This is a close-up image: 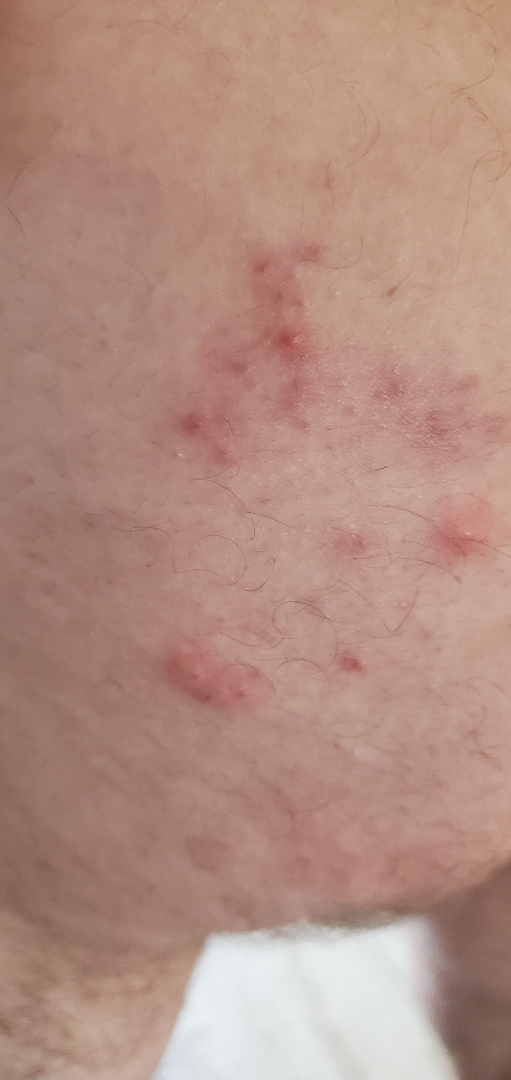differential:
  leading:
    - Folliculitis
  considered:
    - Keratosis pilaris